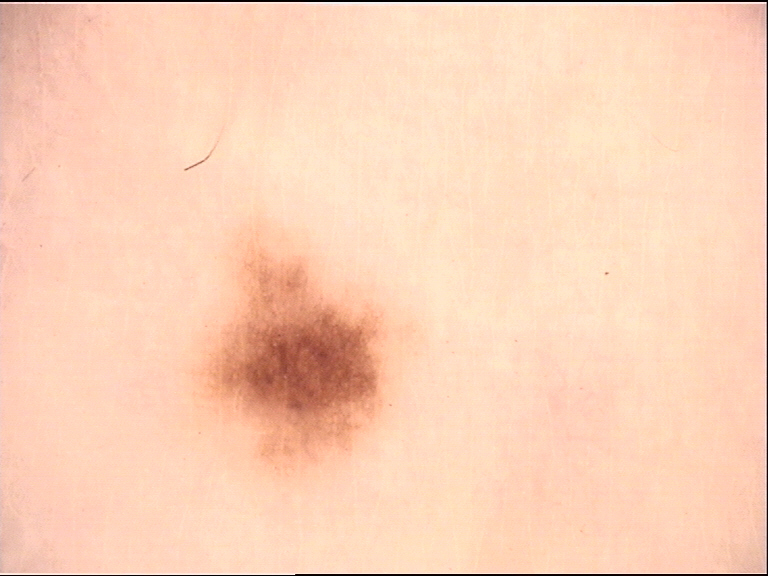A dermatoscopic image of a skin lesion. This is a banal lesion. Classified as a compound nevus.